A dermoscopic image of a skin lesion · a male patient, approximately 85 years of age or older.
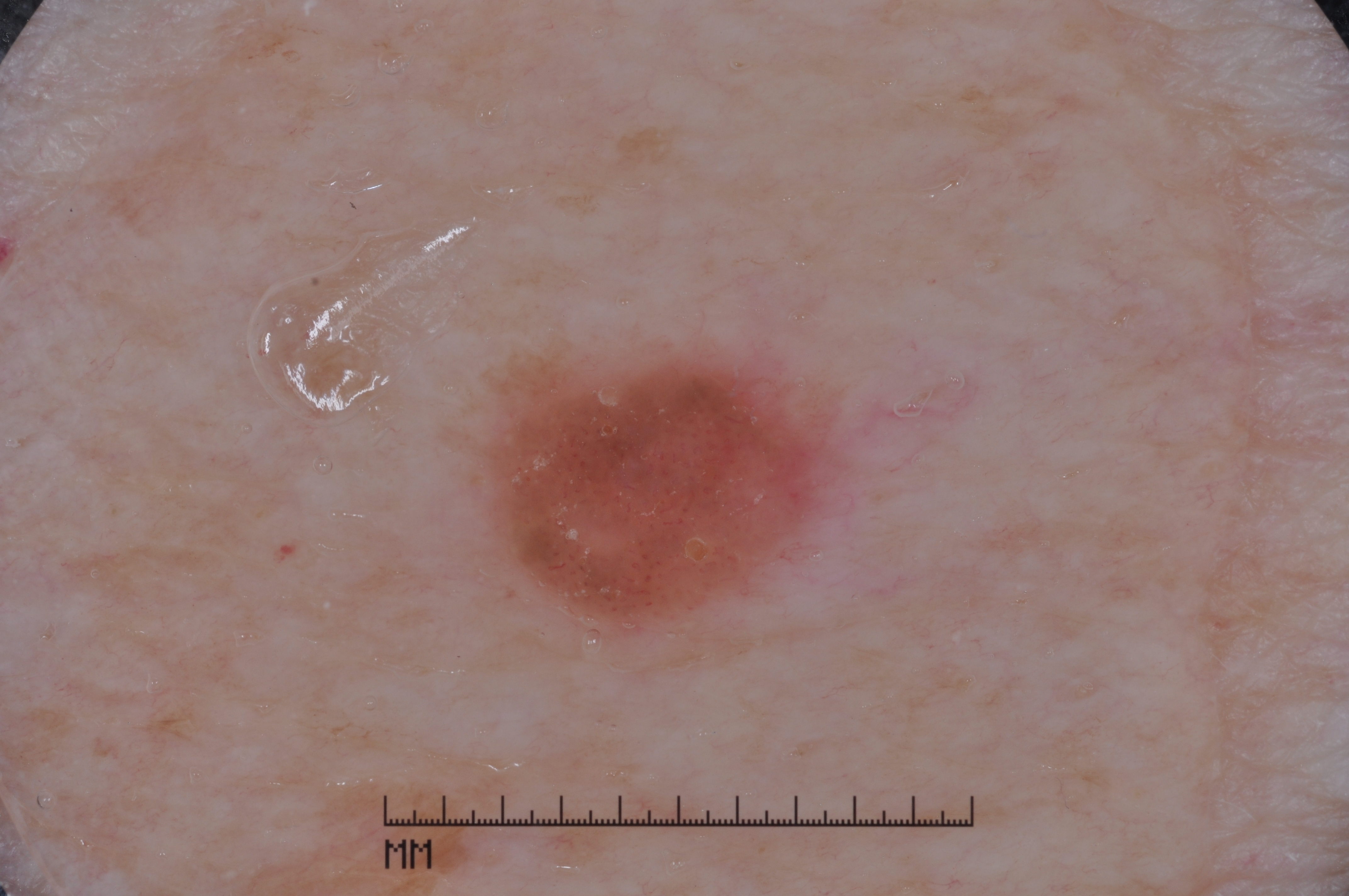<case>
  <lesion_extent>
    <approx_field_fraction_pct>7</approx_field_fraction_pct>
  </lesion_extent>
  <dermoscopic_features>
    <present/>
    <absent>negative network, streaks, pigment network, milia-like cysts</absent>
  </dermoscopic_features>
  <lesion_location>
    <bbox_xyxy>474, 350, 832, 637</bbox_xyxy>
  </lesion_location>
  <diagnosis>
    <name>seborrheic keratosis</name>
    <malignancy>benign</malignancy>
    <lineage>keratinocytic</lineage>
    <provenance>clinical</provenance>
  </diagnosis>
</case>